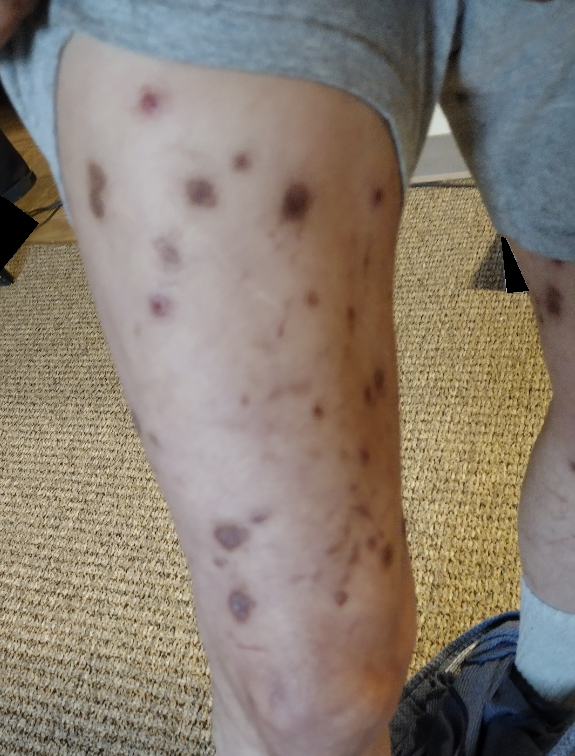The case was indeterminate on photographic review.